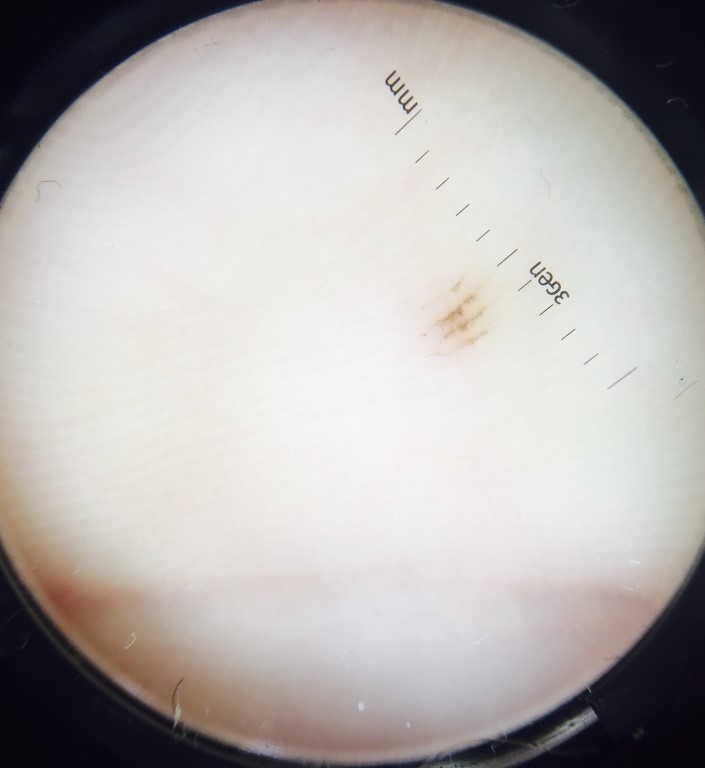• modality: dermatoscopy
• label: acral junctional nevus (expert consensus)